A dermoscopy image of a single skin lesion; a male patient, aged 53 to 57:
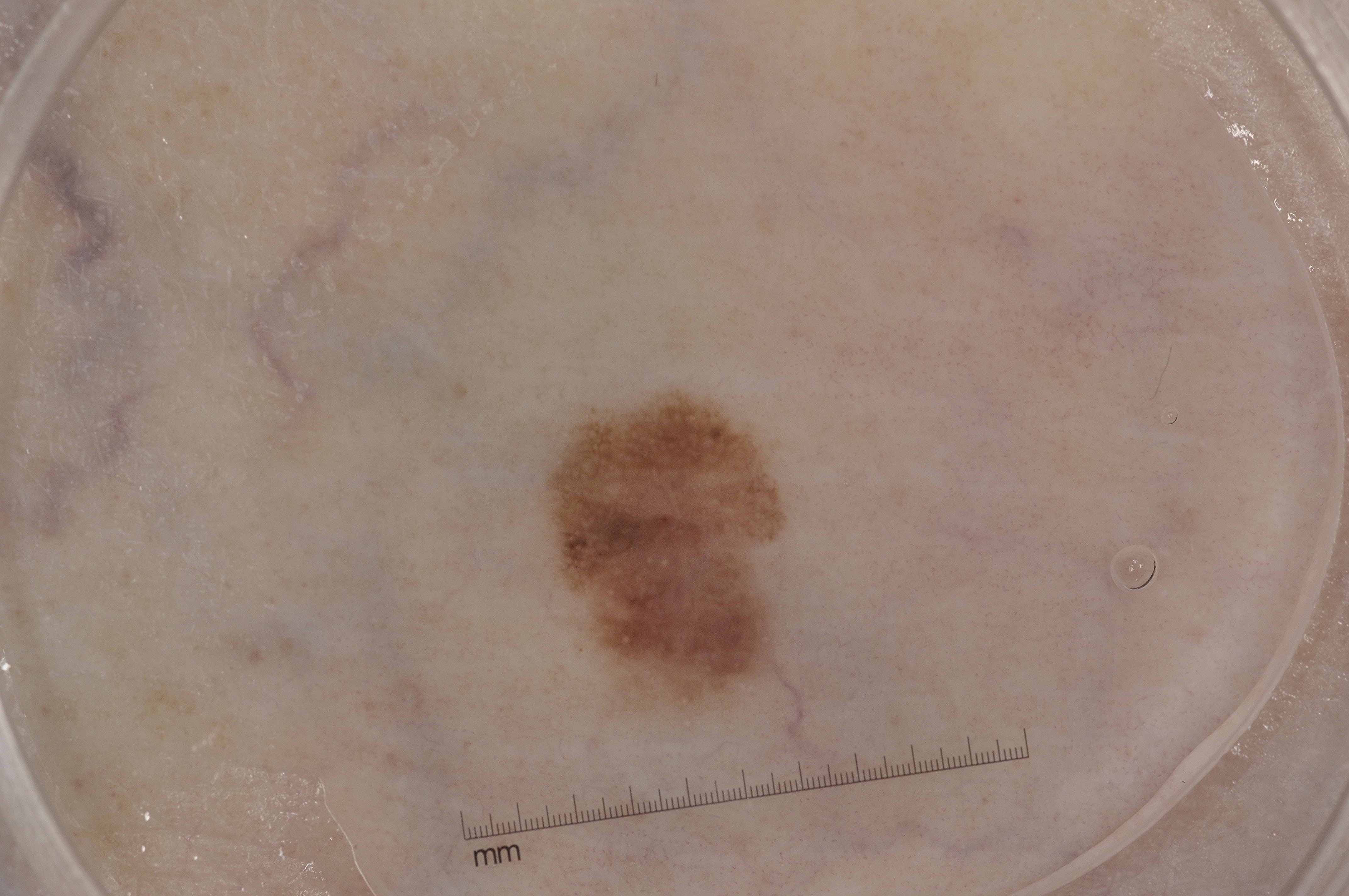Dermoscopically, the lesion shows pigment network and milia-like cysts; no streaks or negative network. The lesion is located at bbox=[534, 387, 795, 719]. On biopsy, the diagnosis was a melanoma.